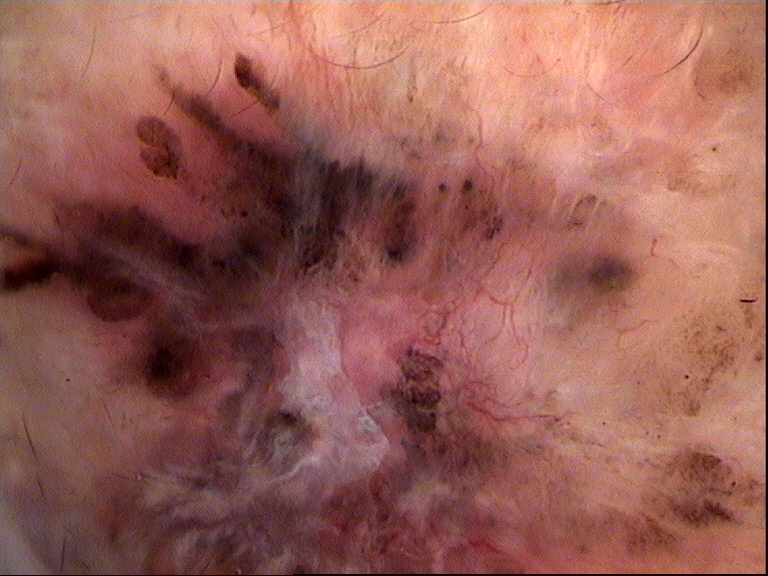Conclusion:
Histopathology confirmed a basal cell carcinoma.